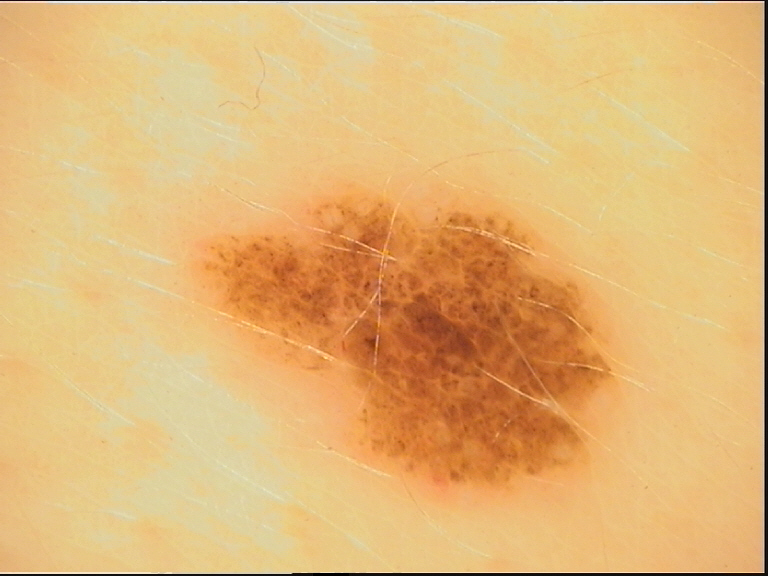Findings:
- image type: dermatoscopy
- diagnostic label: dysplastic compound nevus (expert consensus)